A dermoscopic photograph of a skin lesion:
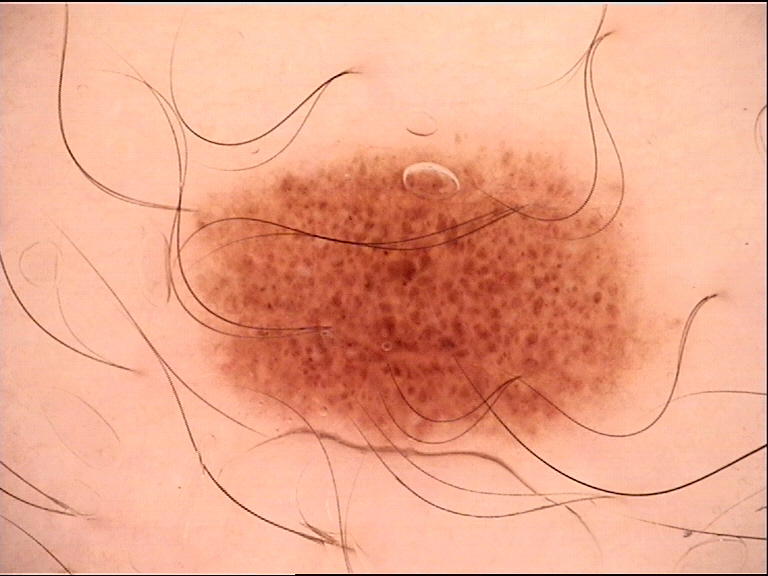The diagnosis was a dysplastic junctional nevus.